The patient notes the condition has been present for less than one week; the lesion involves the arm; the patient is 40–49, female; this image was taken at a distance: 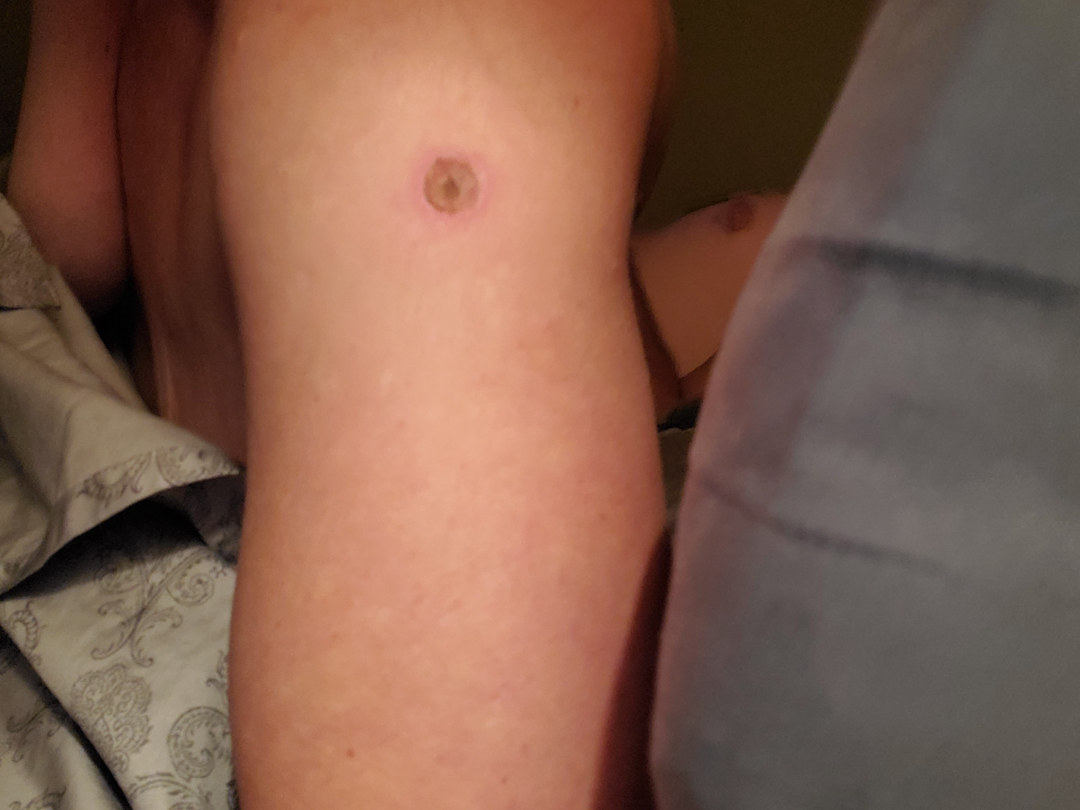Ecthyma (favored); Chronic ulcer of skin (possible); Skin lesion in drug addict (possible).